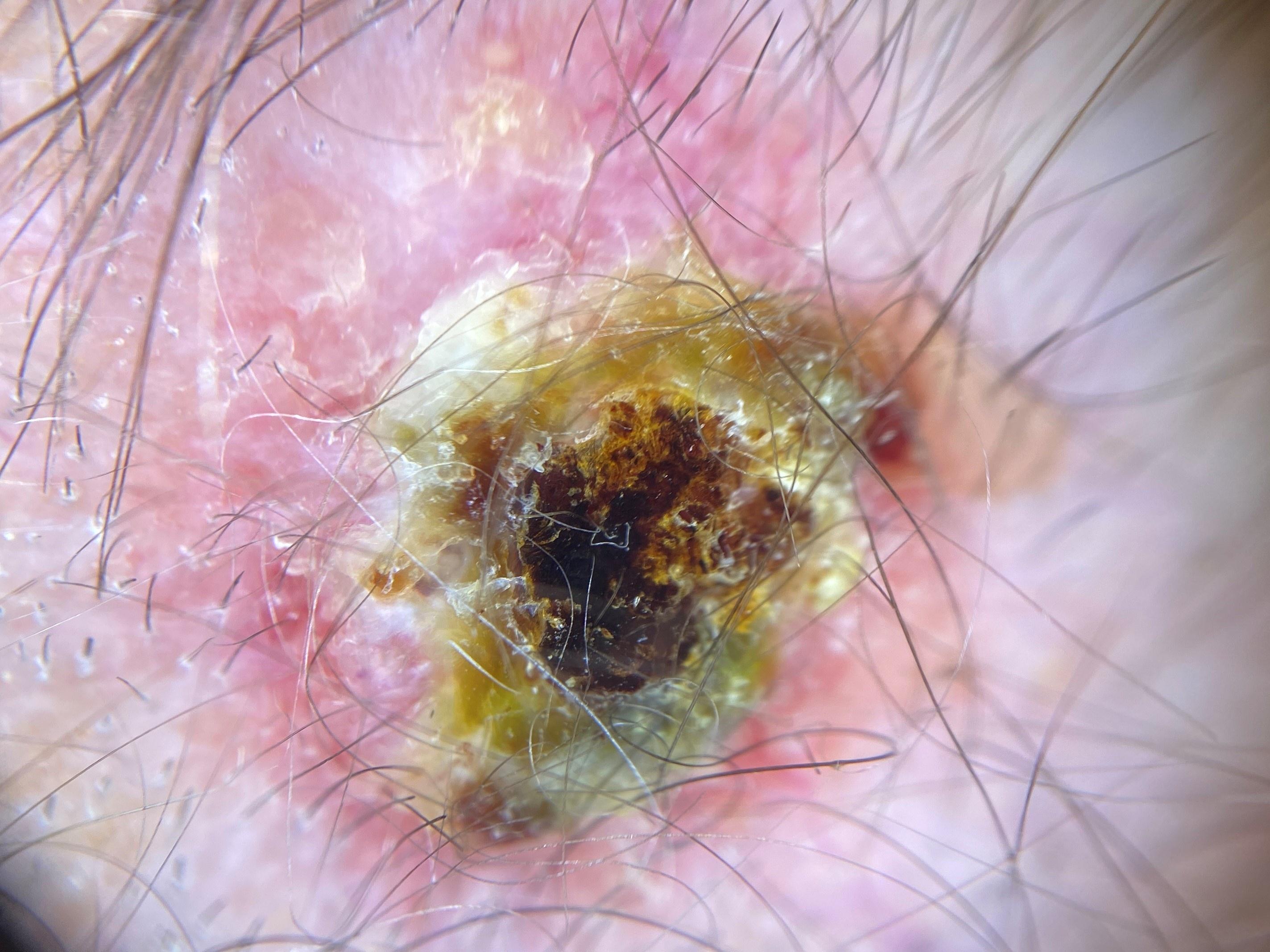Findings: A female subject aged 58-62. The lesion is on the head or neck. Pathology: Biopsy-confirmed as a basal cell carcinoma.